The lesion is described as fluid-filled and raised or bumpy, the lesion is associated with bothersome appearance, the arm is involved, the photograph was taken at a distance:
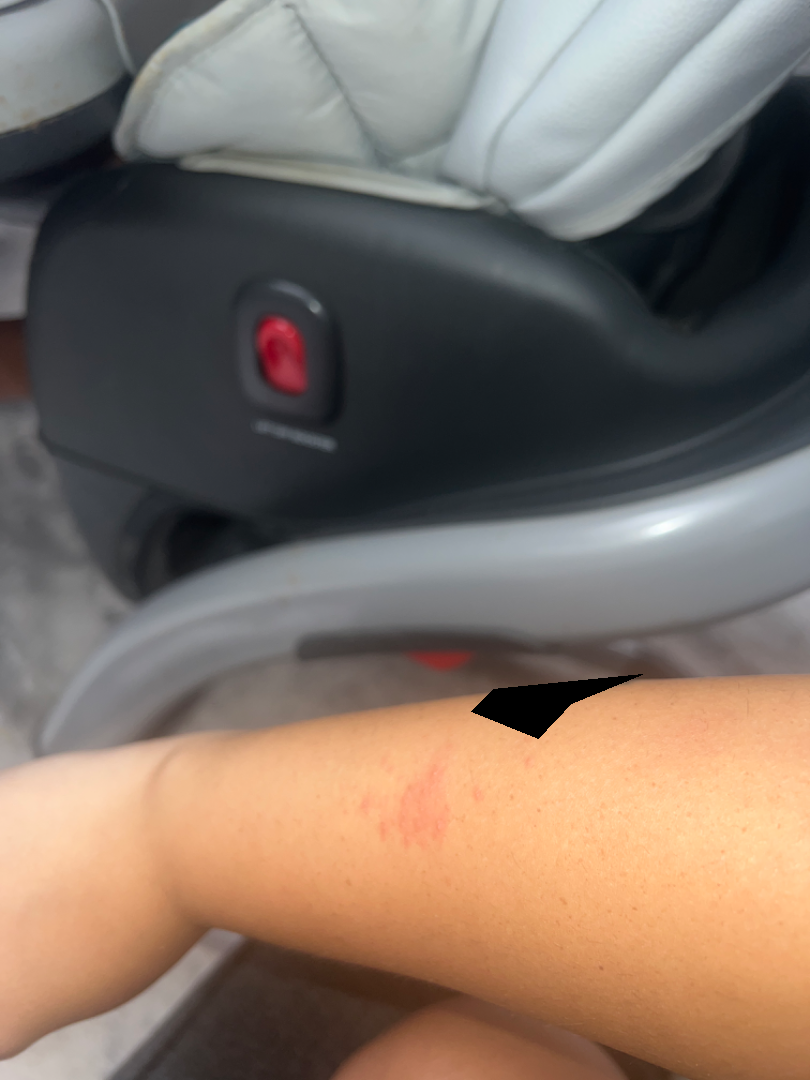assessment — indeterminate